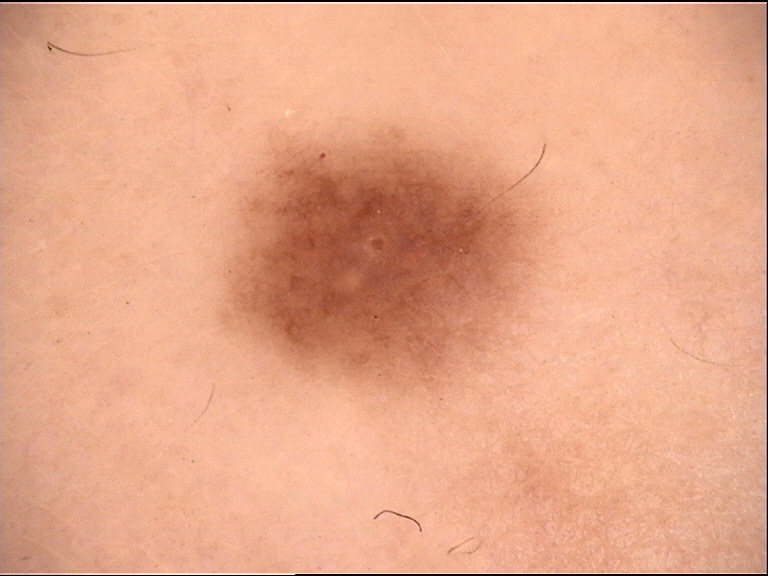<dermoscopy>
  <diagnosis>
    <name>dysplastic junctional nevus</name>
    <code>jd</code>
    <malignancy>benign</malignancy>
    <super_class>melanocytic</super_class>
    <confirmation>expert consensus</confirmation>
  </diagnosis>
</dermoscopy>